A dermoscopic image of a skin lesion:
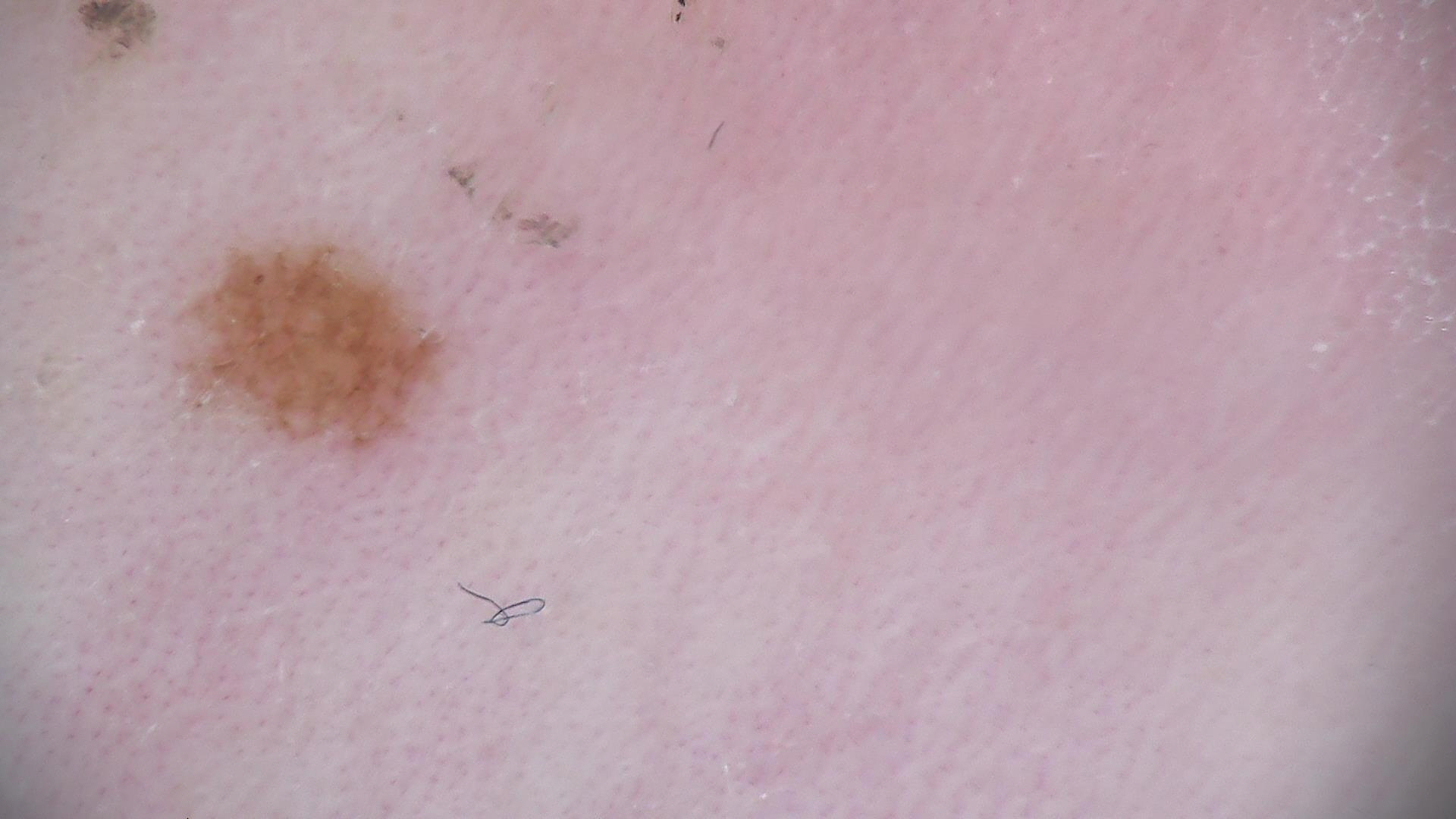The diagnostic label was a banal lesion — a compound nevus.